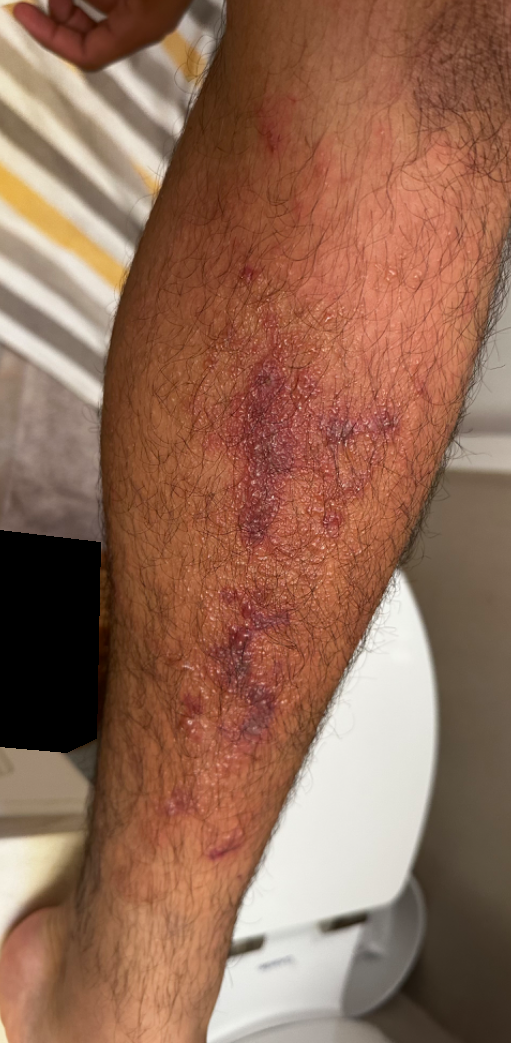– assessment: unable to determine
– shot type: close-up
– site: leg
– patient's own categorization: a rash
– texture: raised or bumpy
– associated systemic symptoms: none reported